The contributor is 50–59, female · the lesion is described as raised or bumpy · the photograph was taken at an angle.
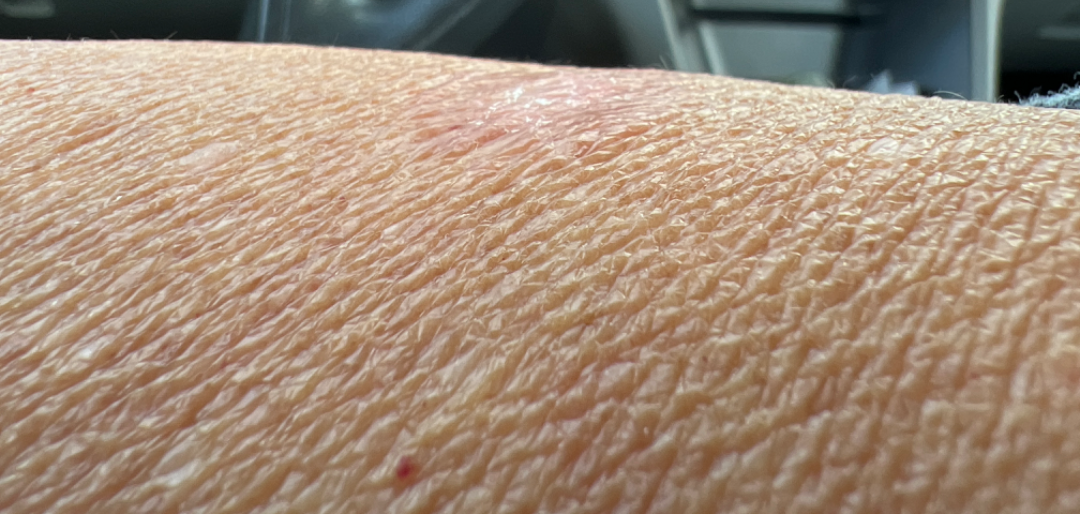The reviewer was unable to grade this case for skin condition.